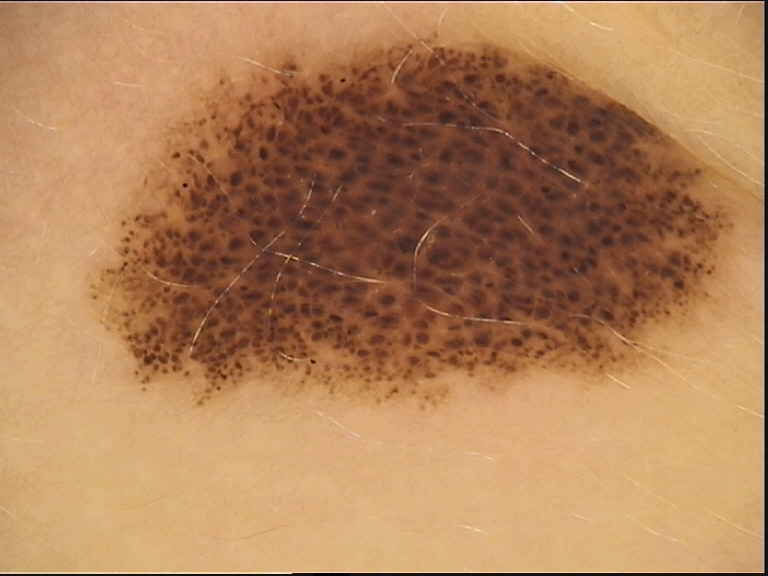Labeled as a compound nevus.